A male subject in their mid-80s or older; the patient was assessed as Fitzpatrick phototype I; a skin lesion imaged with contact-polarized dermoscopy: 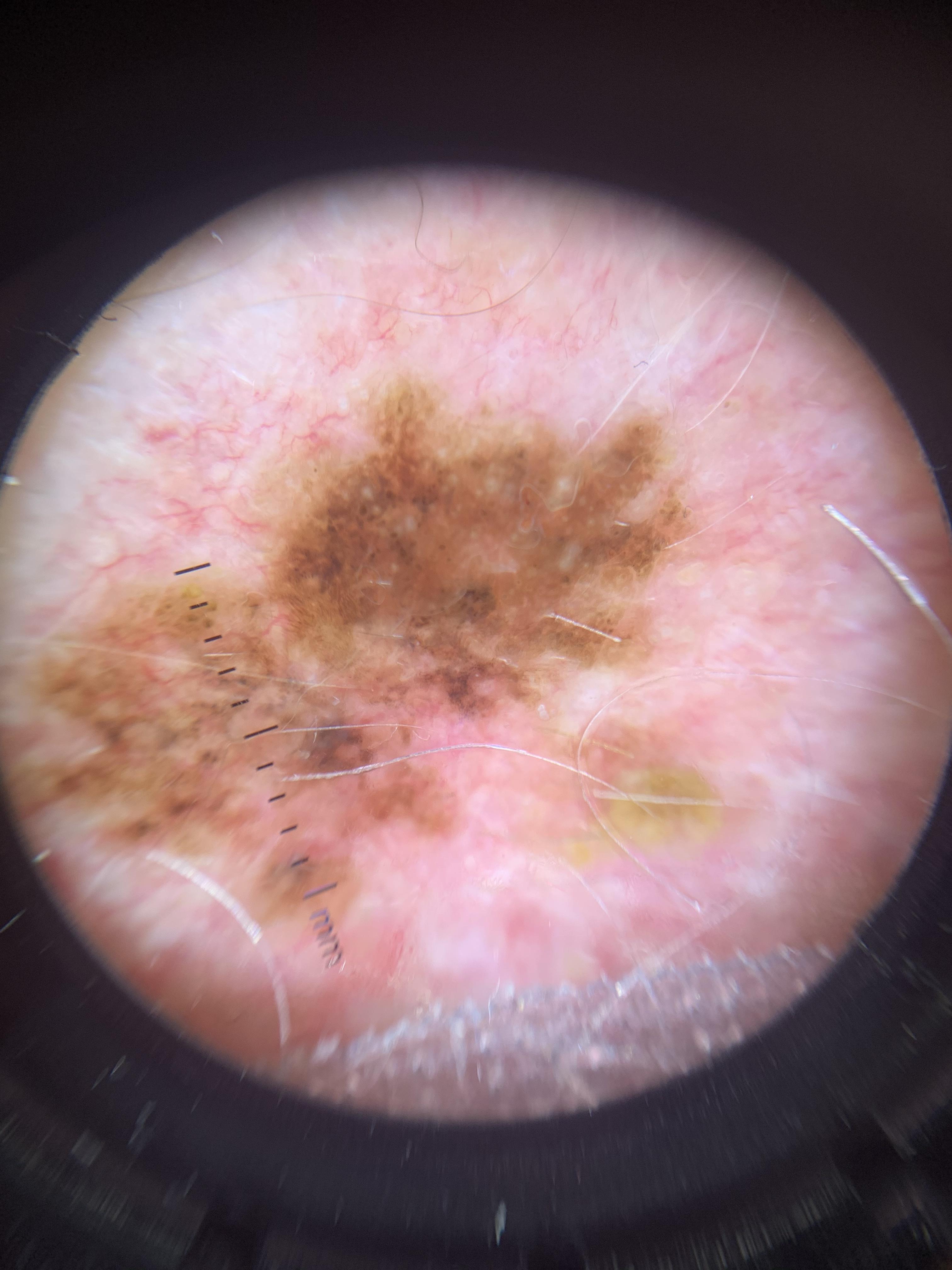Notes:
– body site — the head or neck
– diagnostic label — Melanoma (biopsy-proven)